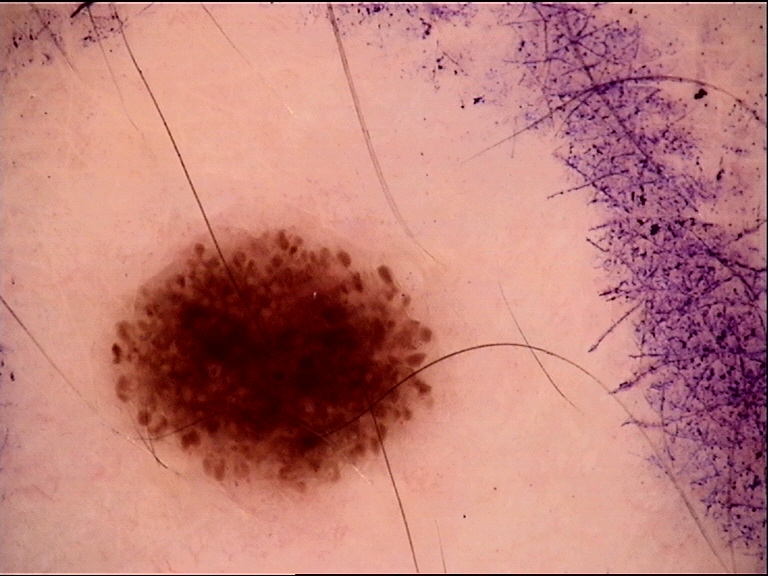<dermoscopy>
<image>dermoscopy</image>
<diagnosis>
<name>dysplastic junctional nevus</name>
<code>jd</code>
<malignancy>benign</malignancy>
<super_class>melanocytic</super_class>
<confirmation>expert consensus</confirmation>
</diagnosis>
</dermoscopy>